Collected as part of a research study, without a referral diagnosis. A female subject 50 years of age. A clinical close-up of a skin lesion:
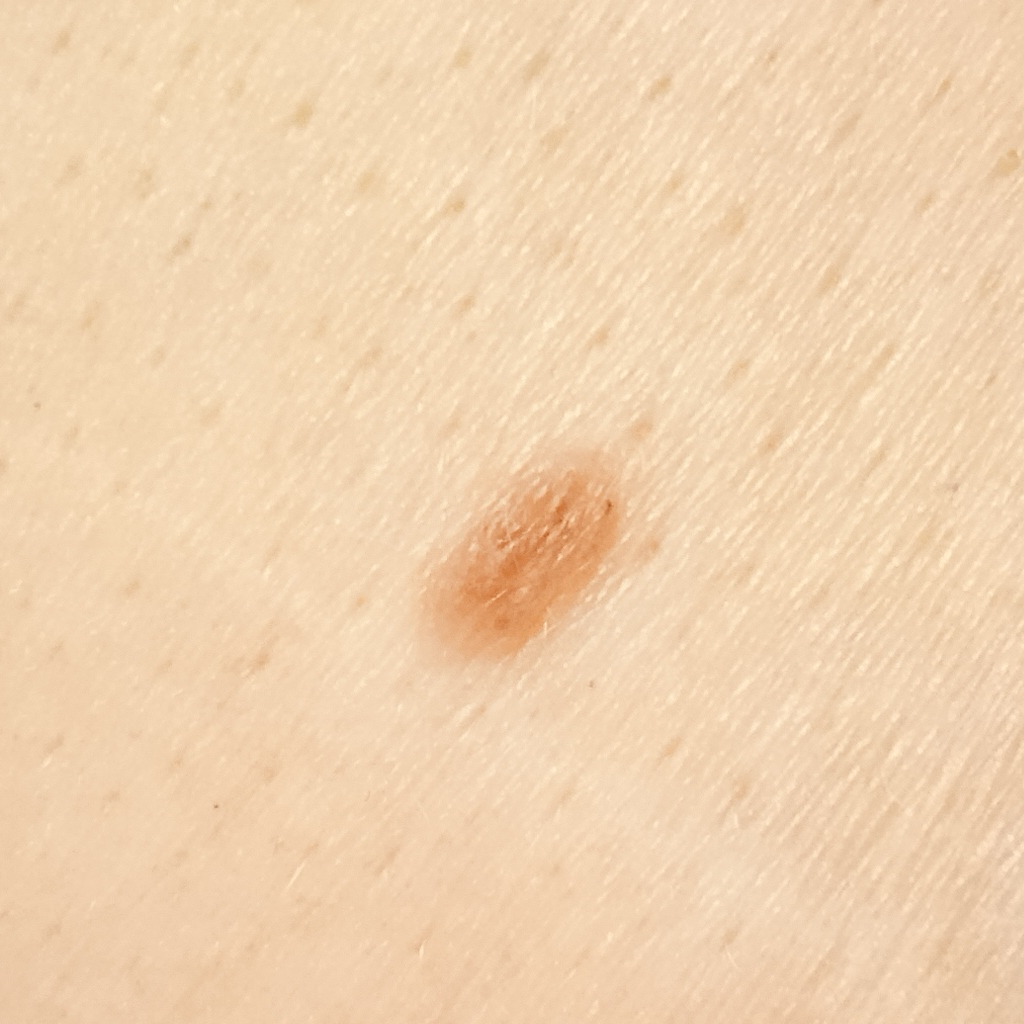site=the torso
diameter=4.9 mm
diagnostic label=melanocytic nevus (dermatologist consensus)